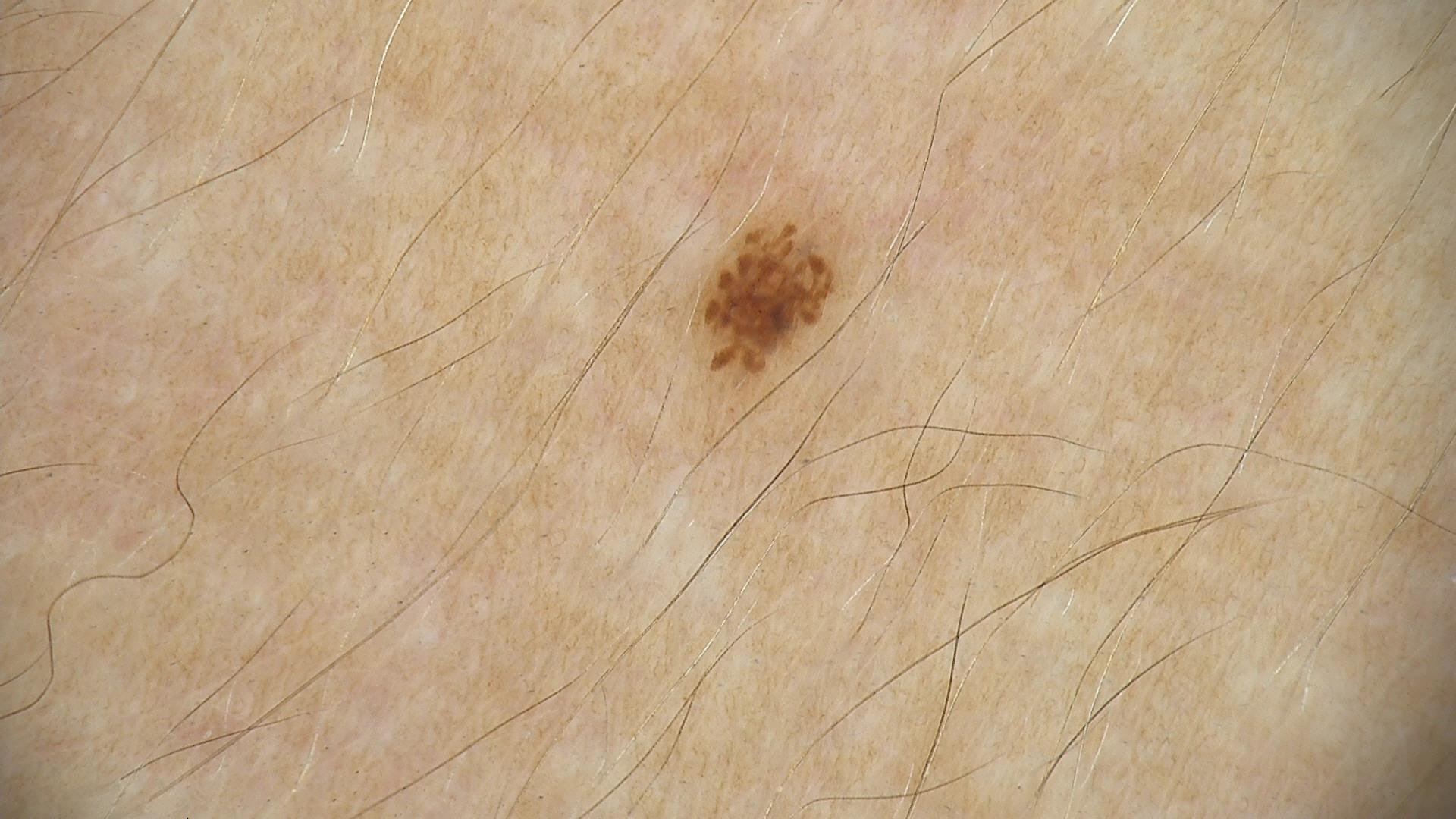Q: What kind of image is this?
A: dermoscopy
Q: What is the diagnosis?
A: dysplastic junctional nevus (expert consensus)